A female patient age 74 · a clinical photograph of a skin lesion.
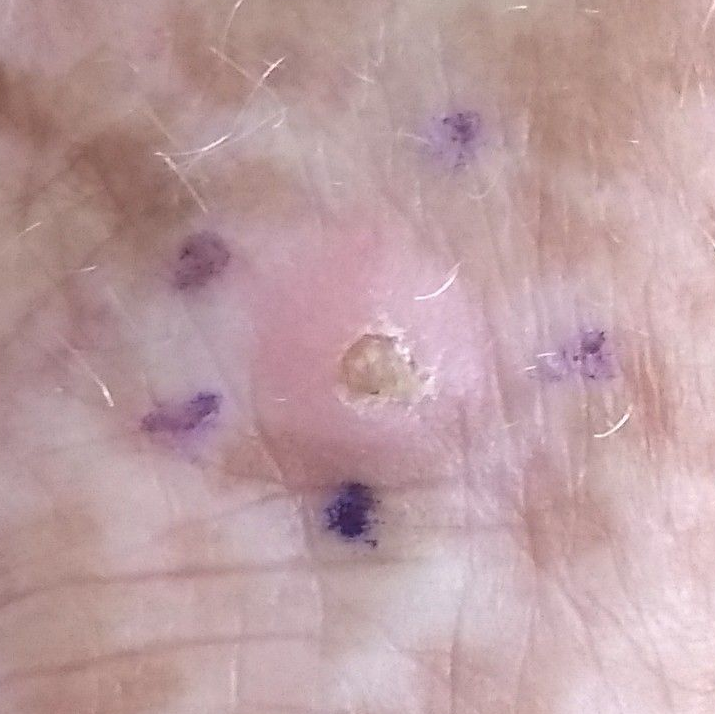The lesion involves a hand. Per patient report, the lesion is elevated and itches, but has not bled and has not grown. Histopathology confirmed an actinic keratosis.